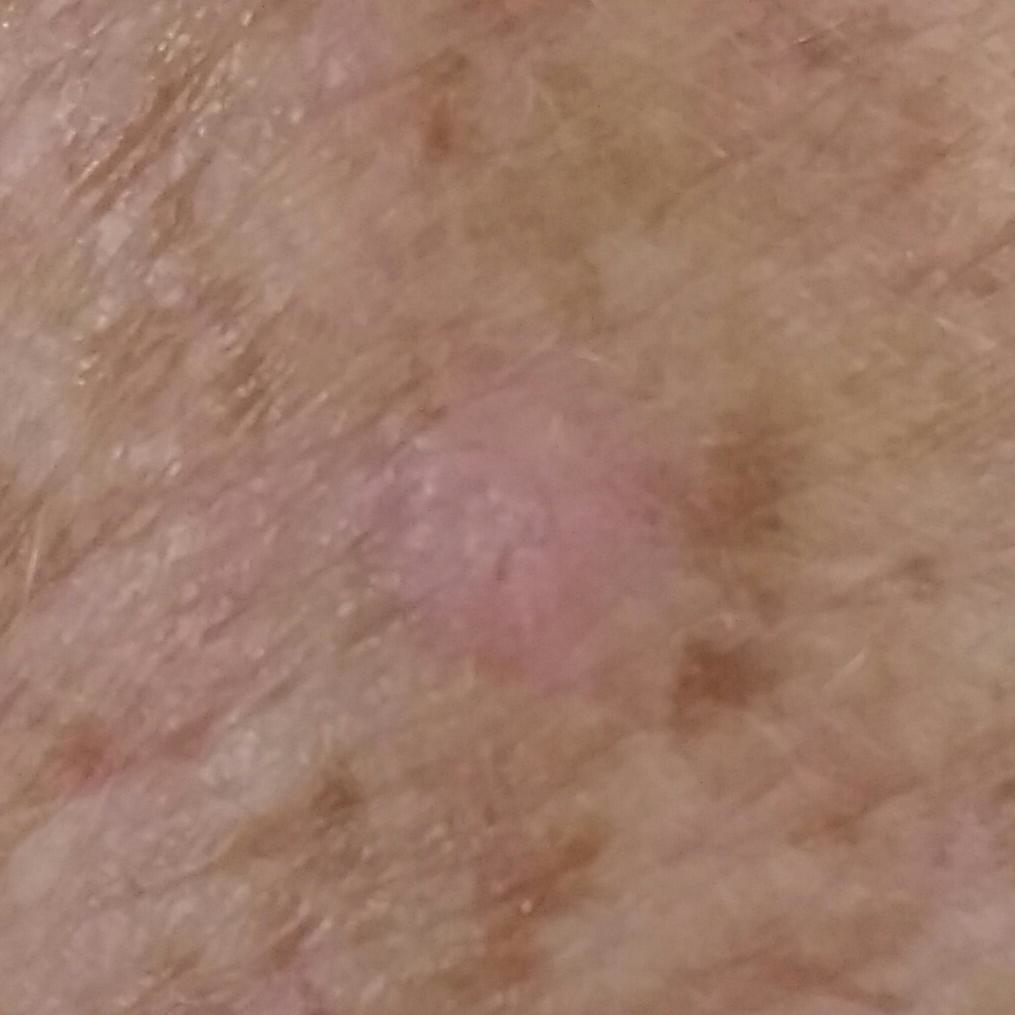Q: Who is the patient?
A: 69 years of age
Q: How was this image acquired?
A: smartphone clinical photo
Q: What is the anatomic site?
A: a forearm
Q: Any reported symptoms?
A: growth, itching
Q: What was the clinical impression?
A: actinic keratosis (clinical consensus)